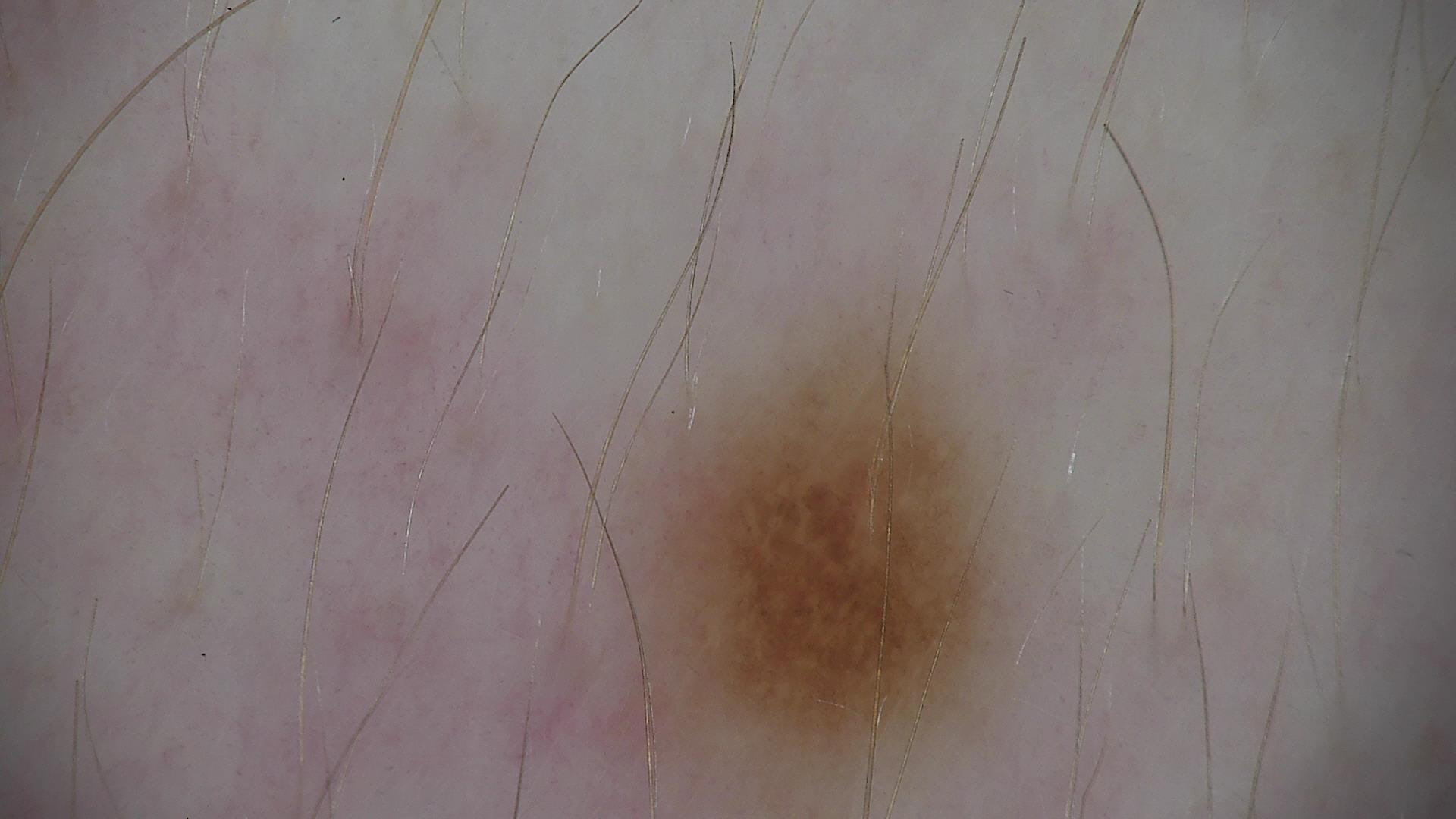A dermoscopy image of a single skin lesion. Diagnosed as a benign lesion — a dysplastic junctional nevus.